This image was taken at a distance. The affected area is the head or neck.
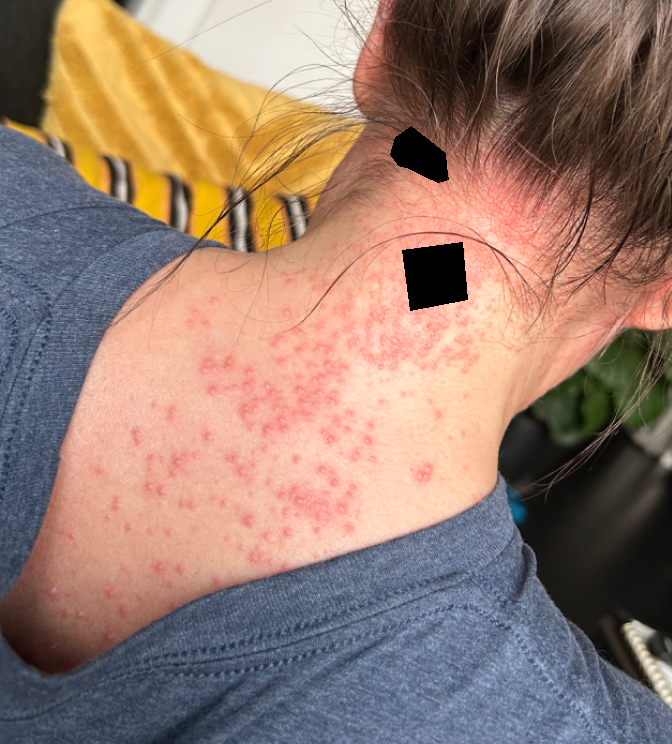The case was indeterminate on photographic review.